A clinical photograph showing a skin lesion; by history, prior skin cancer (patient or family), pesticide exposure, and prior malignancy (patient or family); Fitzpatrick phototype III; a female subject age 74.
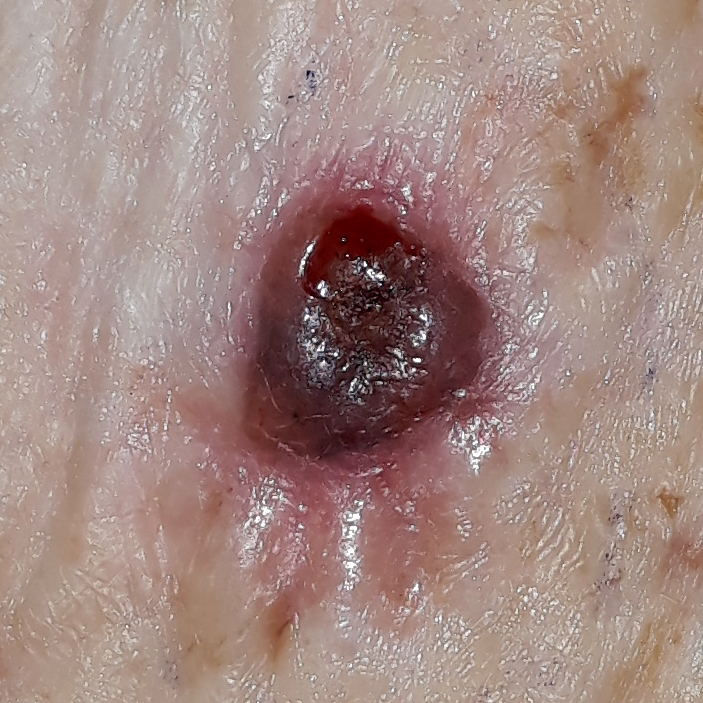The lesion involves an arm. The lesion is roughly 7 by 6 mm. The patient describes that the lesion has bled, hurts, is elevated, itches, and has grown, but has not changed. Histopathological examination showed a basal cell carcinoma.